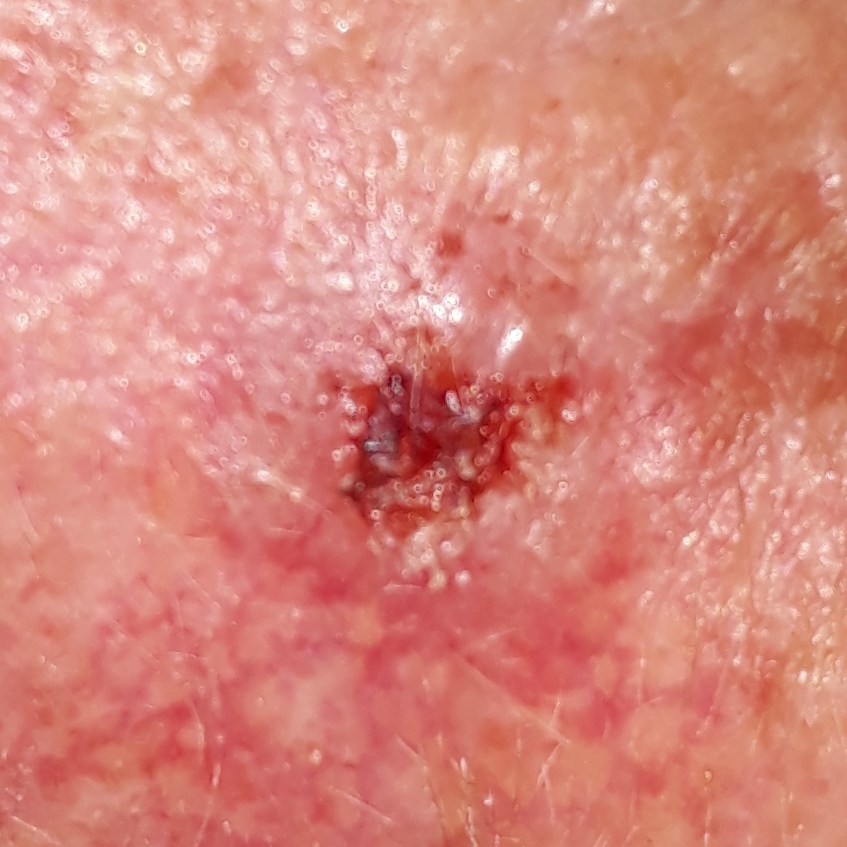Q: Who is the patient?
A: male, aged 53
Q: What is the patient's skin type?
A: IV
Q: Any relevant history?
A: prior skin cancer (patient or family), alcohol use, prior malignancy (patient or family), pesticide exposure, no tobacco use
Q: What kind of image is this?
A: clinical photograph
Q: Where on the body is the lesion?
A: the face
Q: Lesion size?
A: 7x6 mm
Q: What symptoms does the patient report?
A: bleeding, itching, elevation
Q: What is the diagnosis?
A: basal cell carcinoma (biopsy-proven)